A dermoscopic image of a skin lesion: 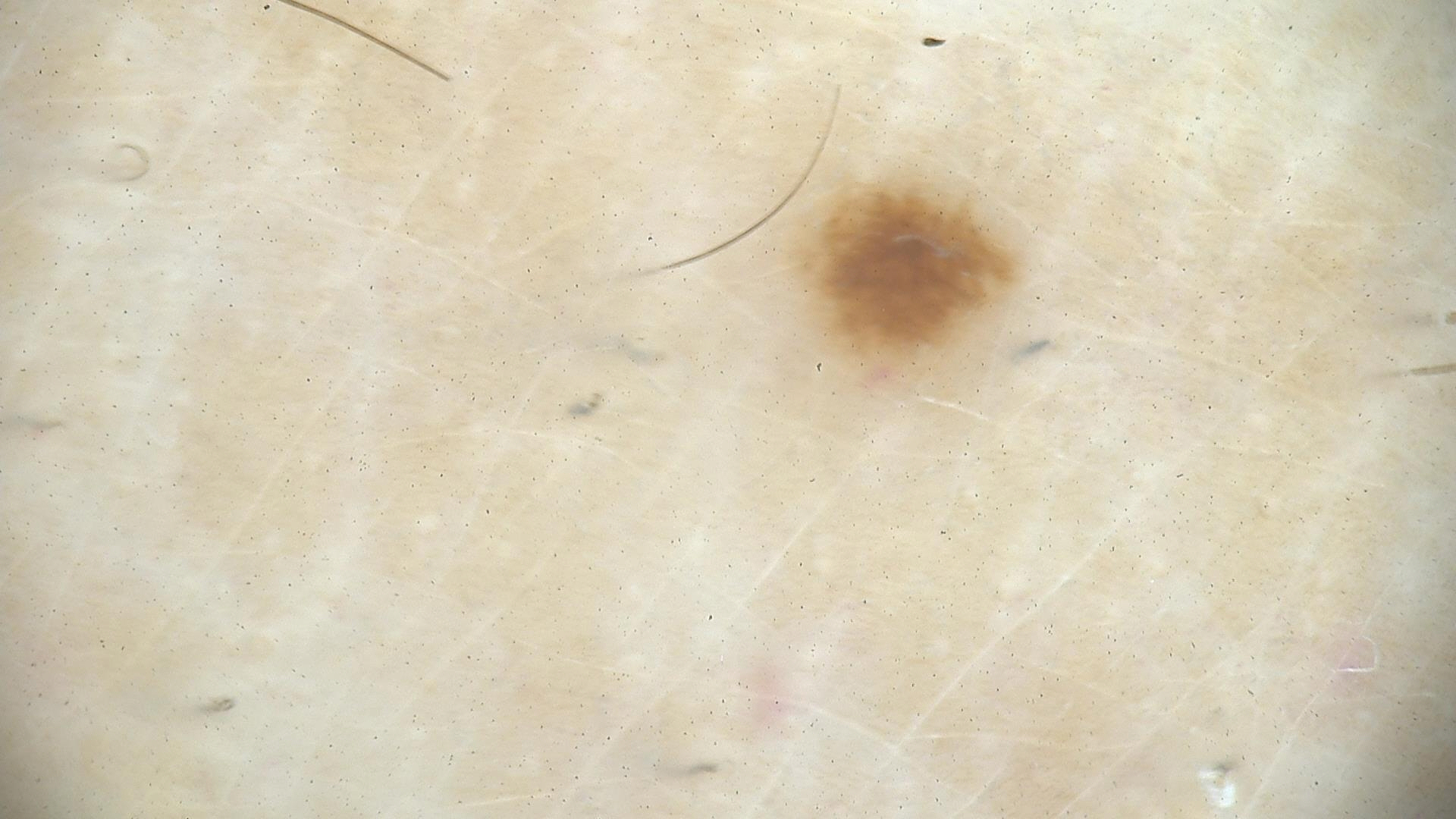Conclusion:
The diagnostic label was a benign lesion — a dysplastic junctional nevus.